A male patient aged 54; dermoscopy of a skin lesion; collected as part of a research study, without a referral diagnosis.
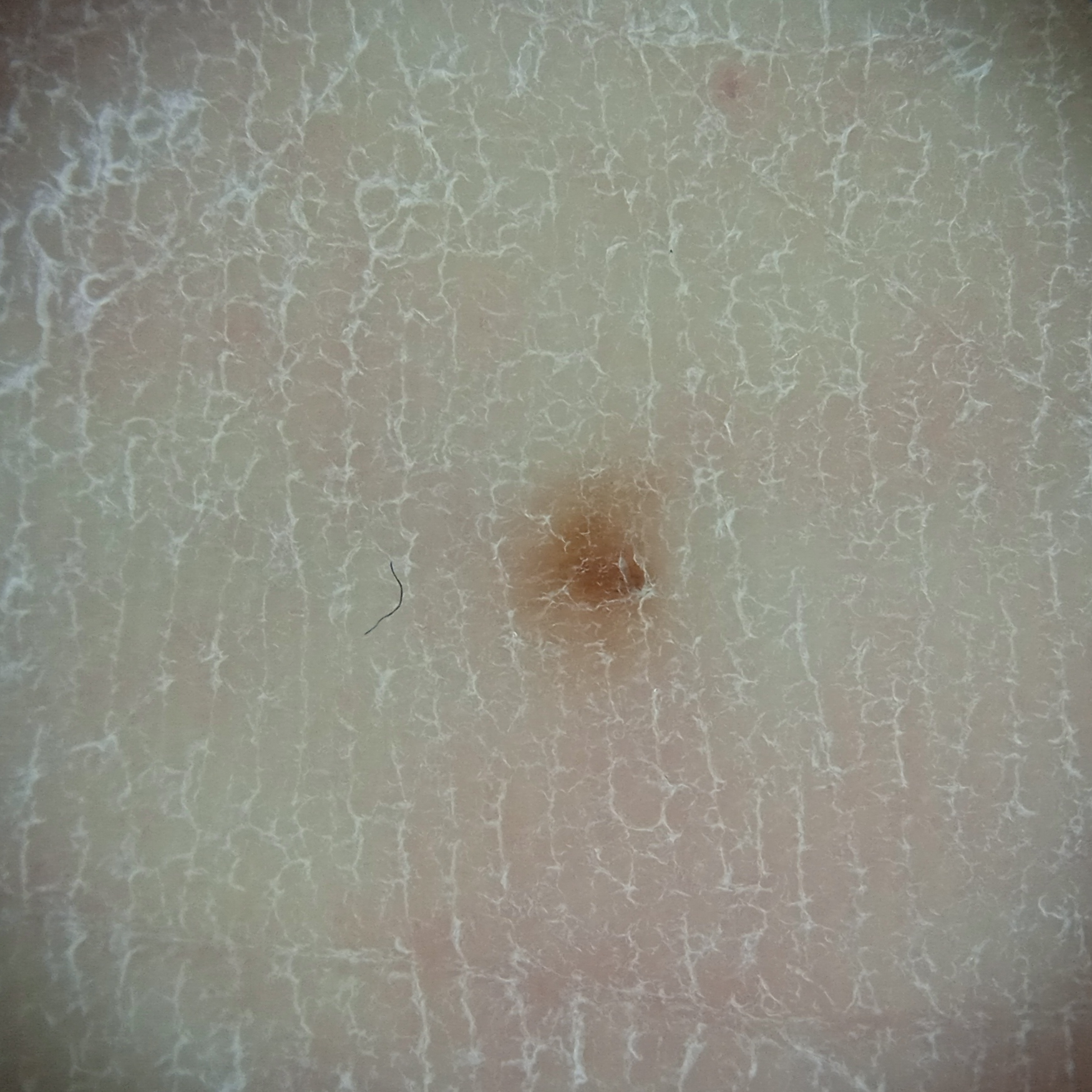anatomic site: a leg, size: 2.2 mm, diagnostic label: melanocytic nevus (dermatologist consensus).